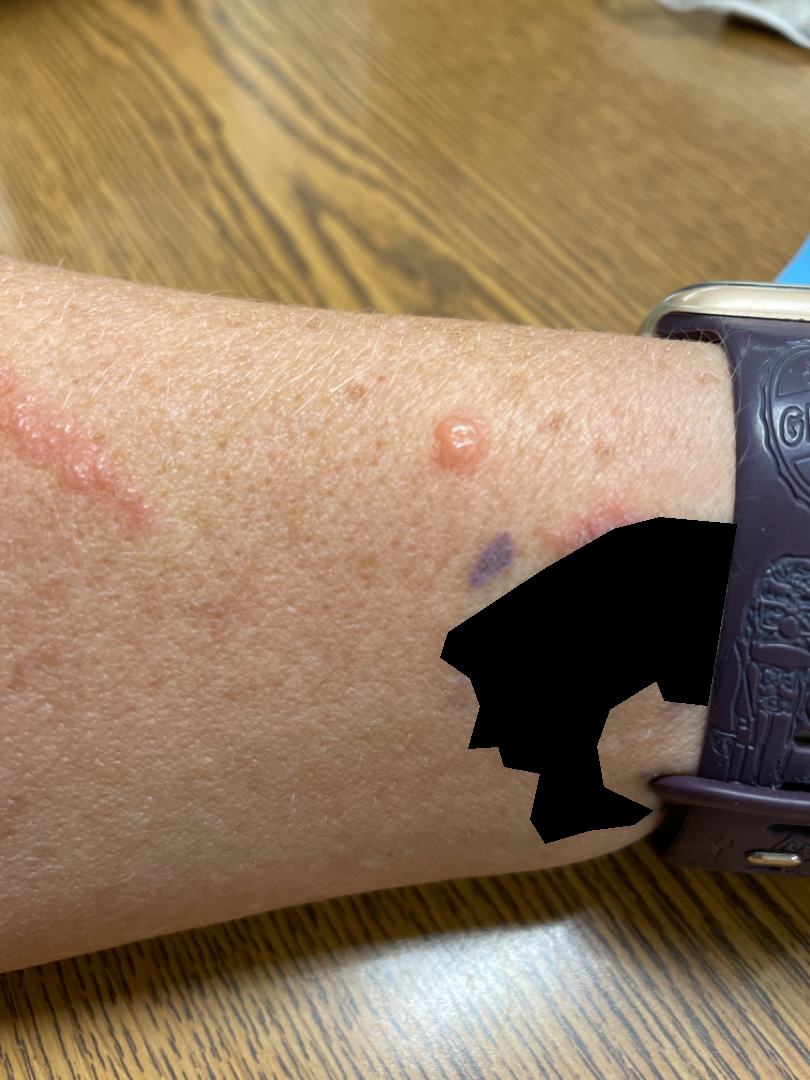Findings: Diagnostic features were not clearly distinguishable in this photograph. Background: Reported duration is one to four weeks. The lesion involves the arm. The photo was captured at an angle. Symptoms reported: itching and enlargement. The subject is 50–59, female. Texture is reported as raised or bumpy.